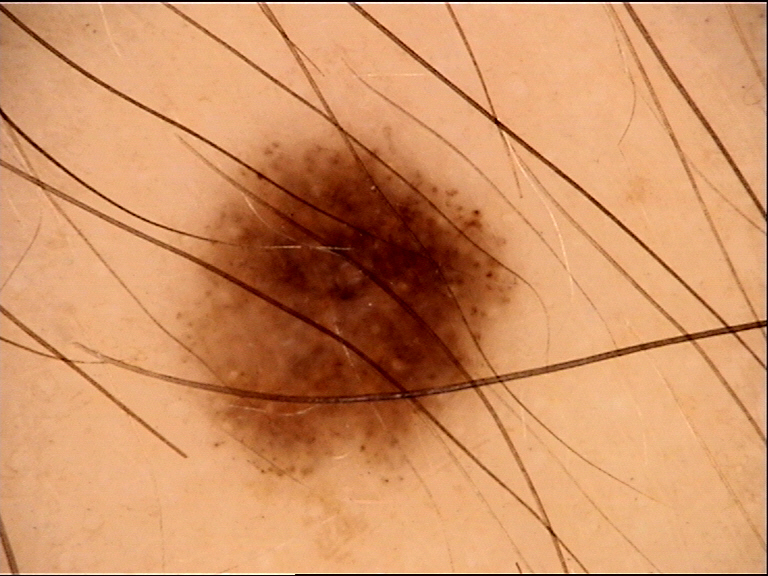imaging: dermoscopy, class: dysplastic junctional nevus (expert consensus).